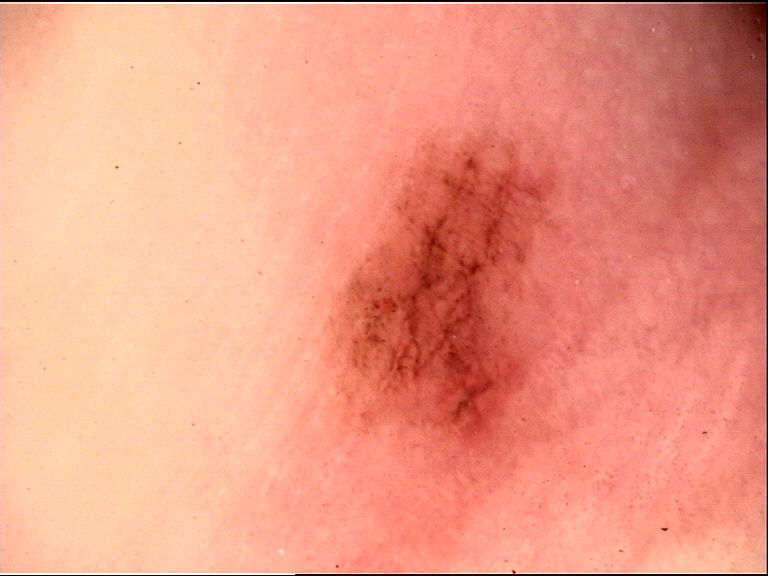Consistent with an acral dysplastic junctional nevus.